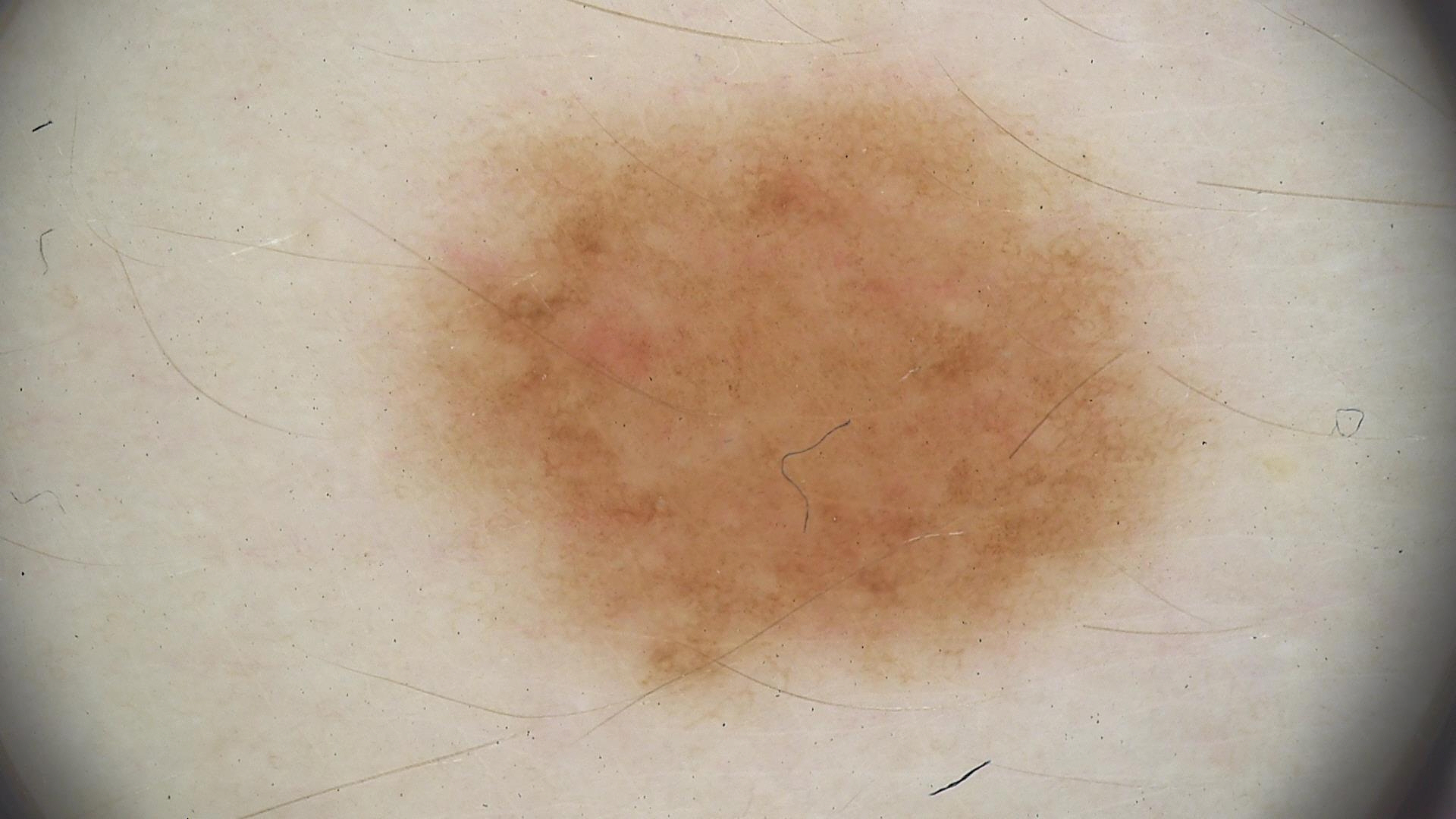Classified as a dysplastic junctional nevus.